This image was taken at a distance. Located on the leg.
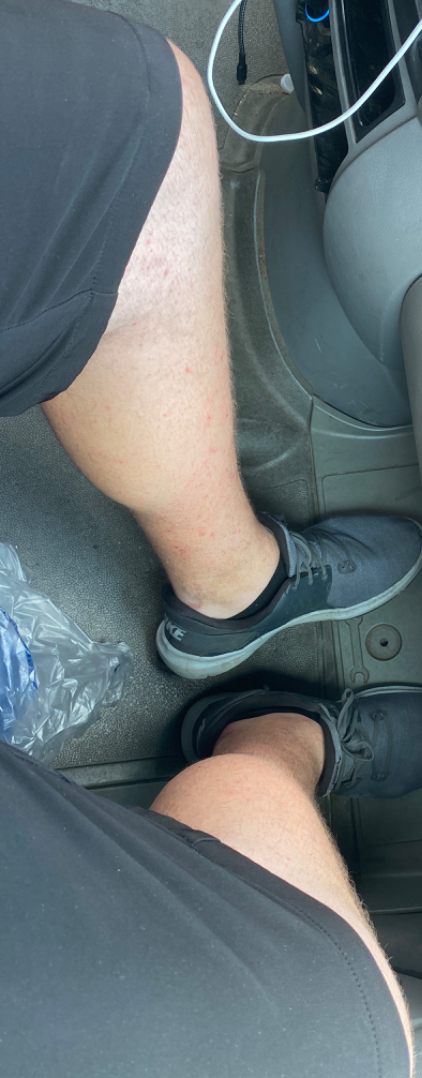The case was indeterminate on photographic review. Self-categorized by the patient as acne. Symptoms reported: bothersome appearance, itching and burning. Texture is reported as raised or bumpy. The condition has been present for less than one week.